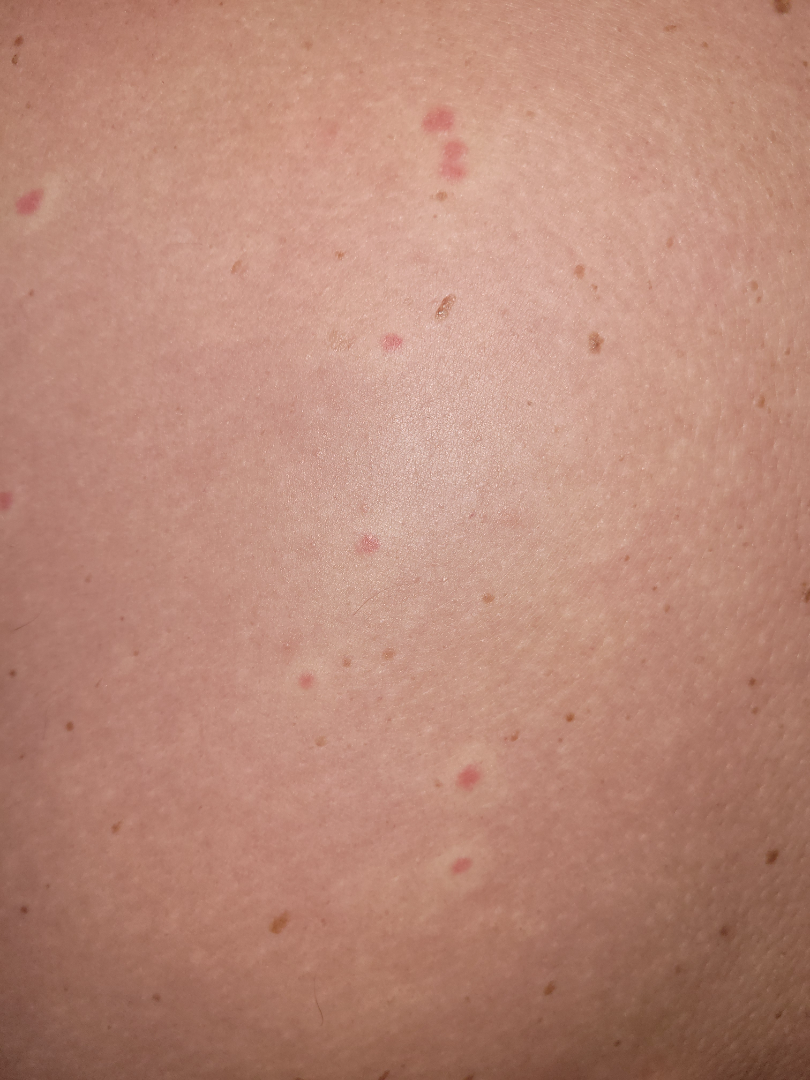Review: Diagnostic features were not clearly distinguishable in this photograph. Patient information: Skin tone: Fitzpatrick phototype III; lay reviewers estimated Monk Skin Tone 2. This is a close-up image.